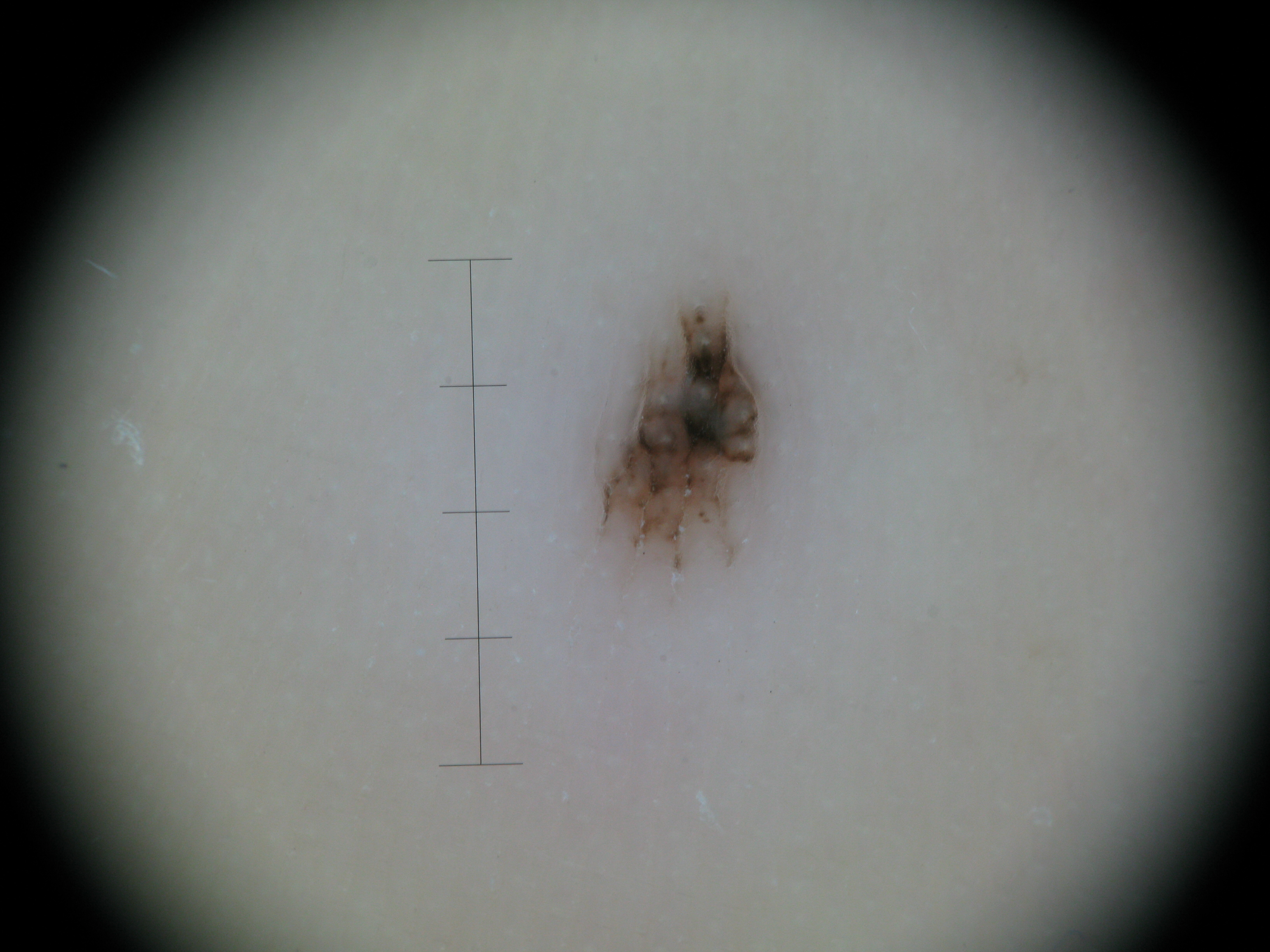modality=dermatoscopy; diagnosis=acral compound nevus (expert consensus).